The patient was assessed as Fitzpatrick phototype V · a clinical photo of a skin lesion taken with a smartphone · by history, pesticide exposure · a female subject aged 57 — 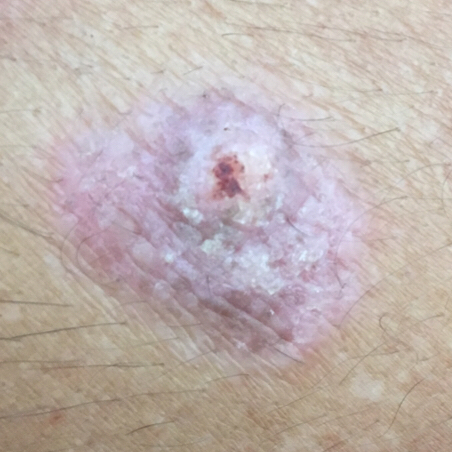Case:
• anatomic site — an arm
• lesion size — 19x18 mm
• symptoms — pain, elevation, growth, itching
• diagnosis — squamous cell carcinoma (biopsy-proven)